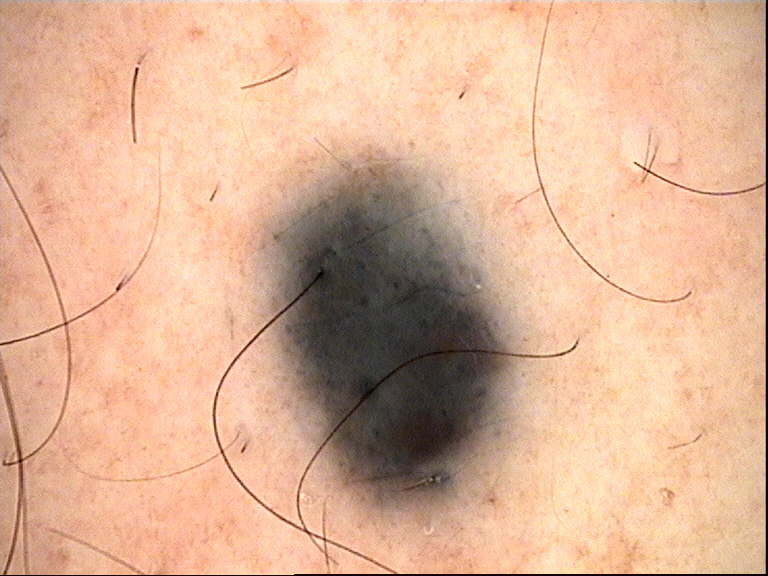class — blue nevus (expert consensus).